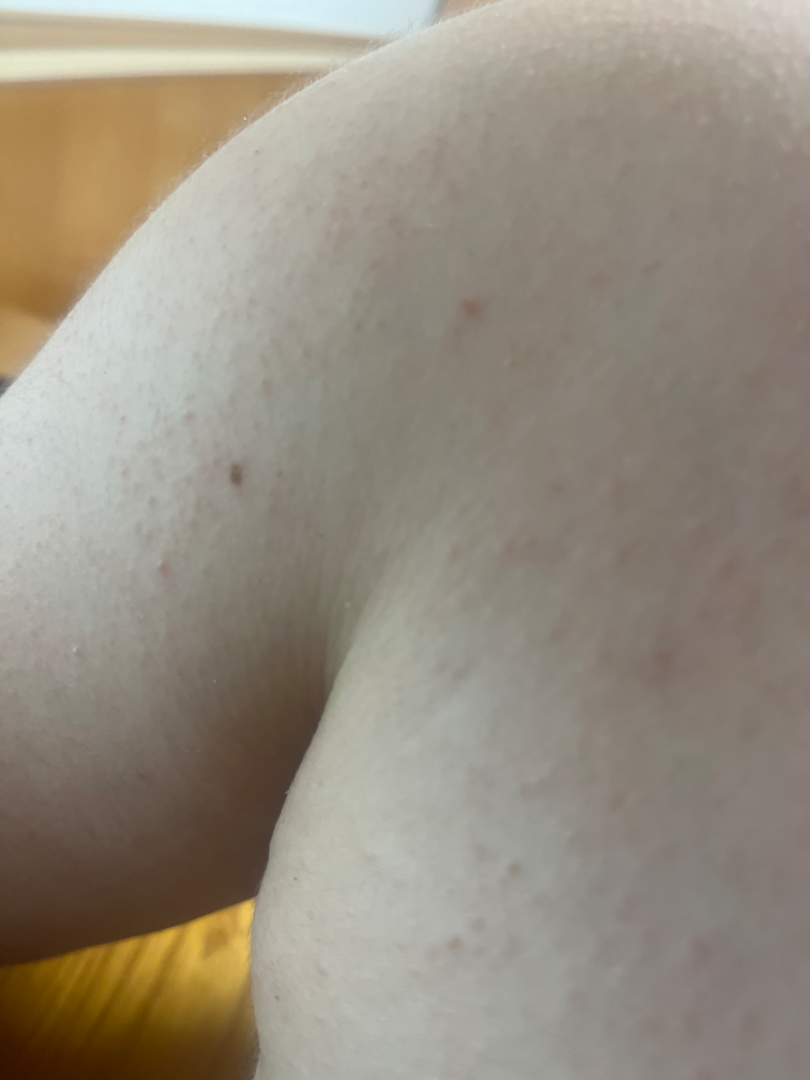The photo was captured at an angle.
The front of the torso, back of the torso and arm are involved.
One reviewing dermatologist: most likely Keratosis pilaris; with consideration of Allergic Contact Dermatitis.